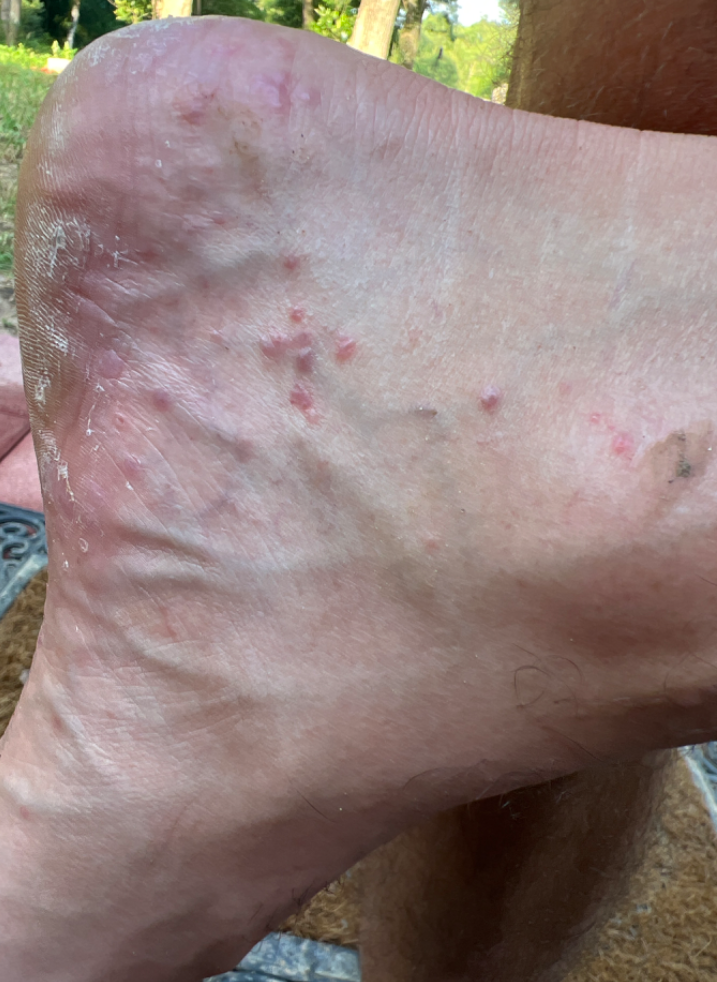assessment — the primary impression is Lichen planus/lichenoid eruption; possibly Insect Bite; with consideration of Allergic Contact Dermatitis.